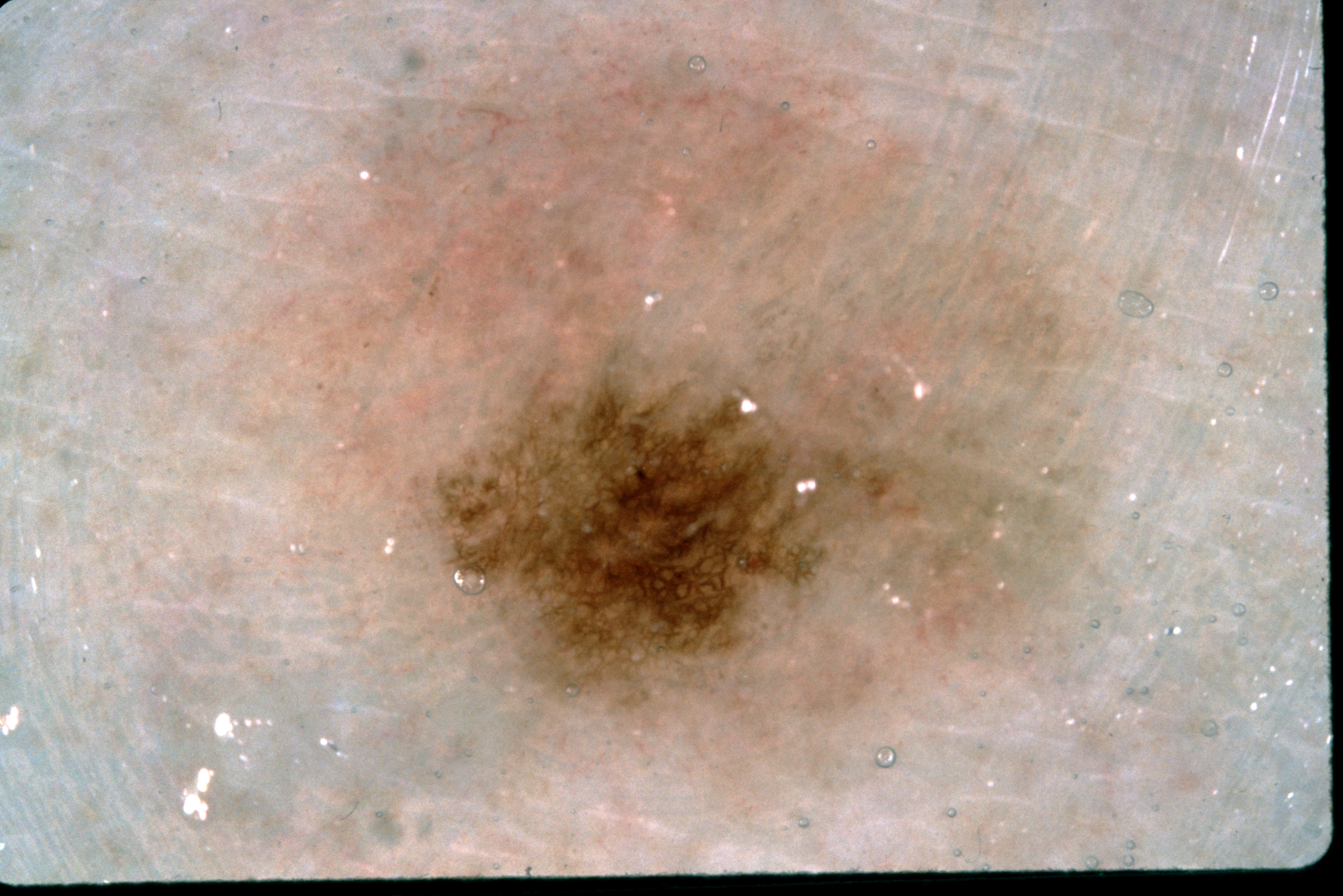Findings:
- patient · female, aged around 35
- image type · dermoscopy
- dermoscopic pattern · pigment network; absent: negative network, milia-like cysts, and streaks
- location · bbox(425, 334, 997, 713)
- size · moderate
- assessment · a melanocytic nevus